A dermatoscopic image of a skin lesion.
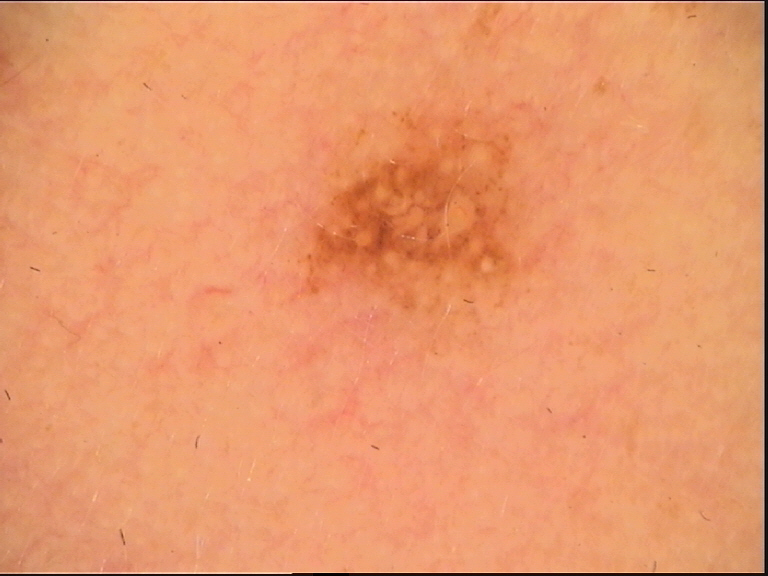The diagnostic label was a dysplastic junctional nevus.